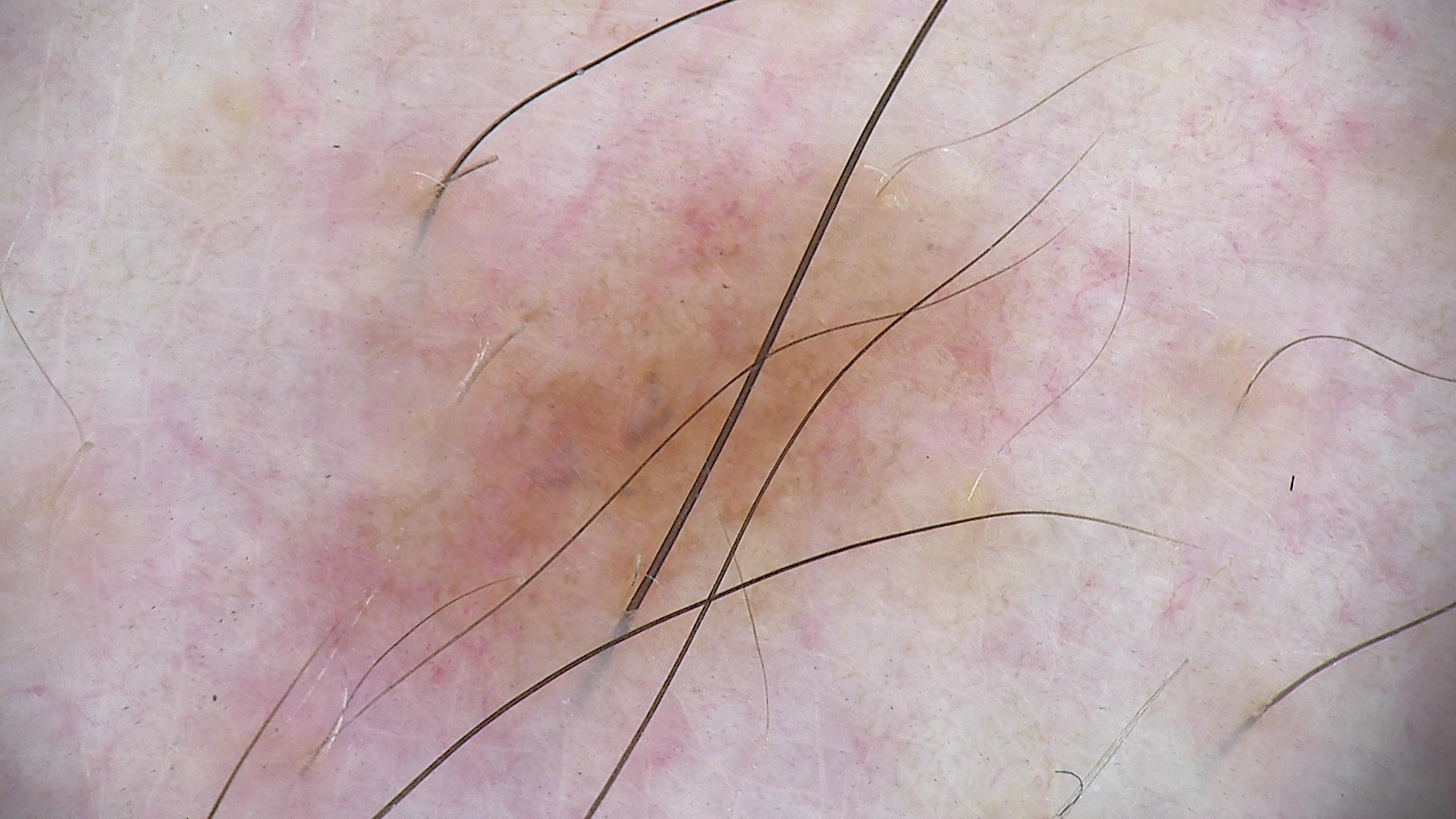A skin lesion imaged with a dermatoscope. The diagnostic label was a benign lesion — a dysplastic junctional nevus.